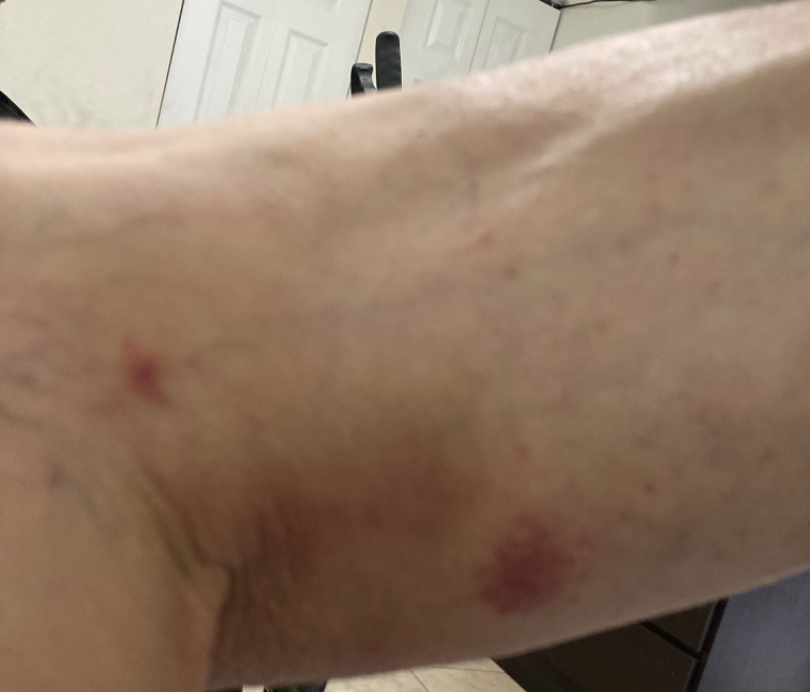The reviewing dermatologist was unable to assign a differential diagnosis from the image. Located on the arm, leg, back of the hand and front of the torso. Male contributor, age 60–69. Close-up view.